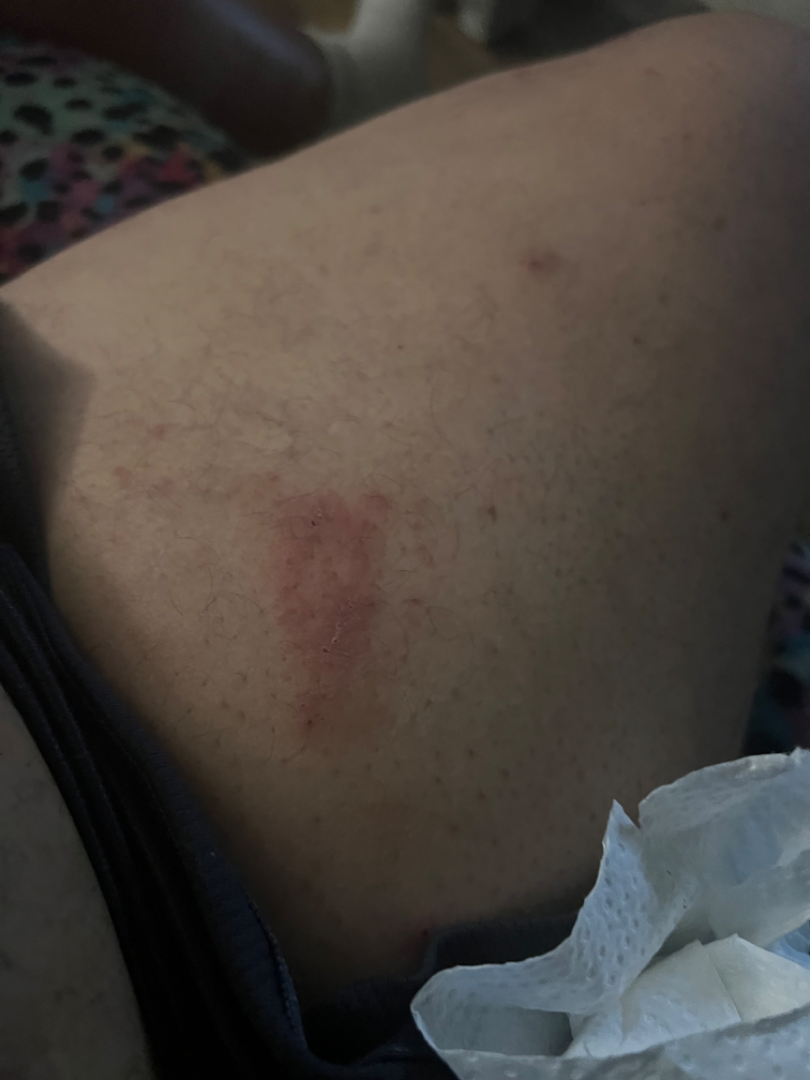| feature | finding |
|---|---|
| assessment | unable to determine |